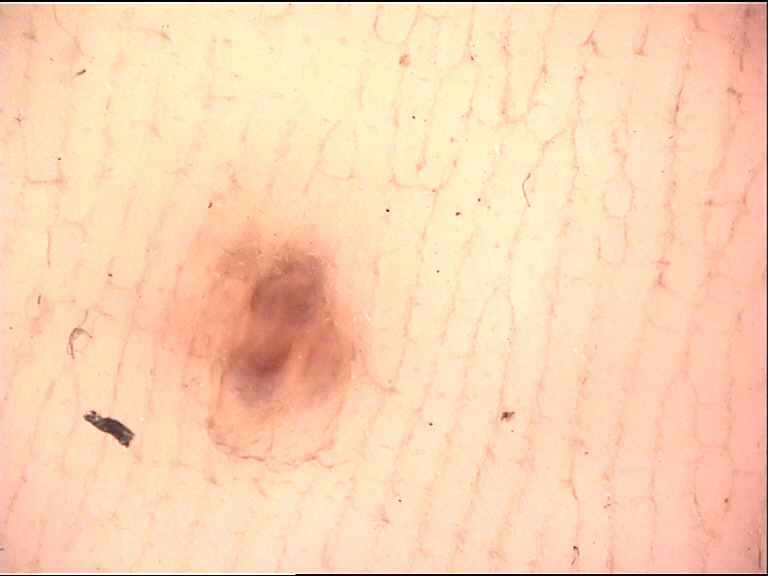Classified as an acral compound nevus.